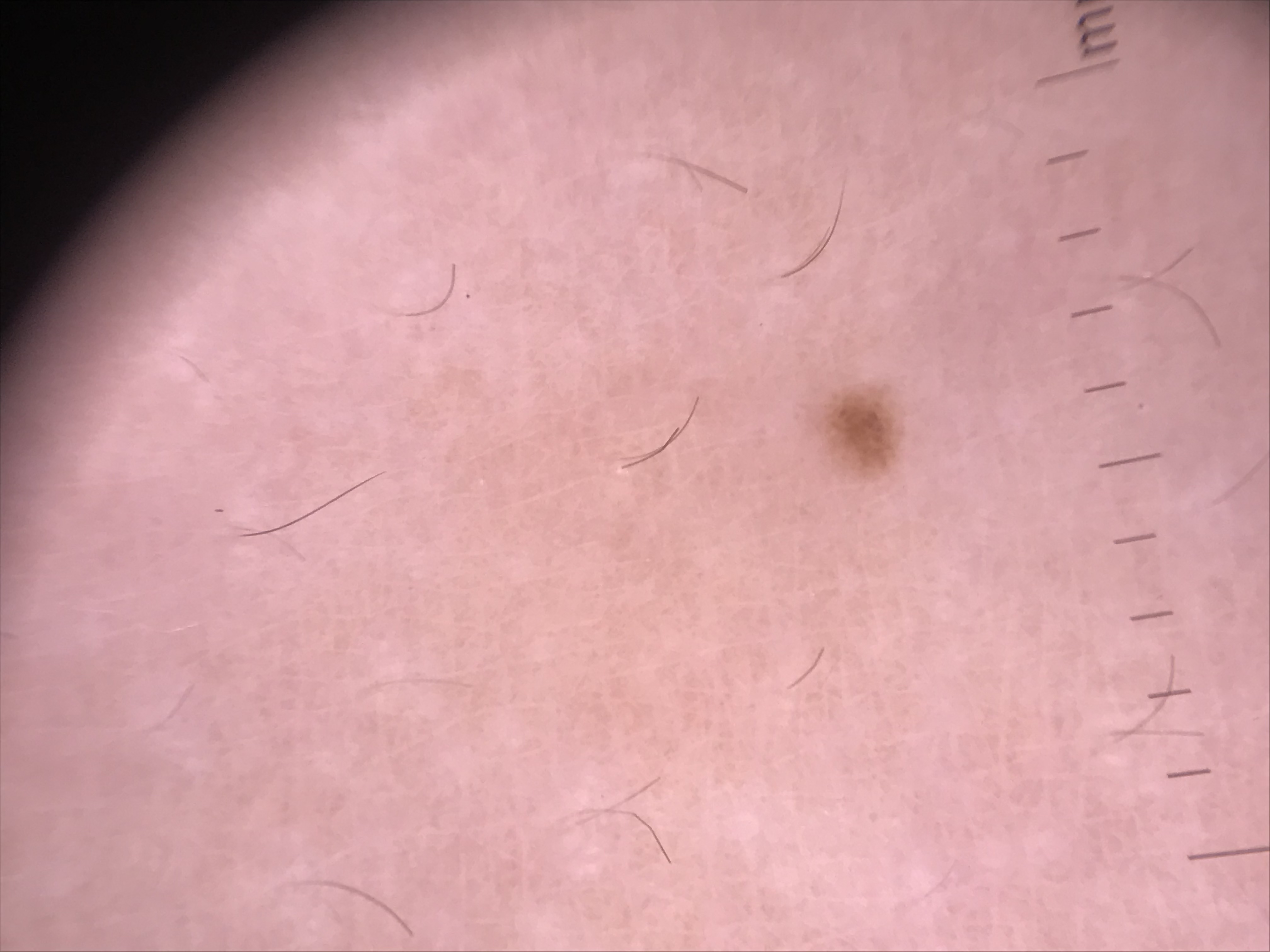diagnosis:
  name: junctional nevus
  code: jb
  malignancy: benign
  super_class: melanocytic
  confirmation: expert consensus